The patient was assessed as skin type II. A dermoscopic close-up of a skin lesion. The chart notes a prior melanoma but no first-degree relative with melanoma.
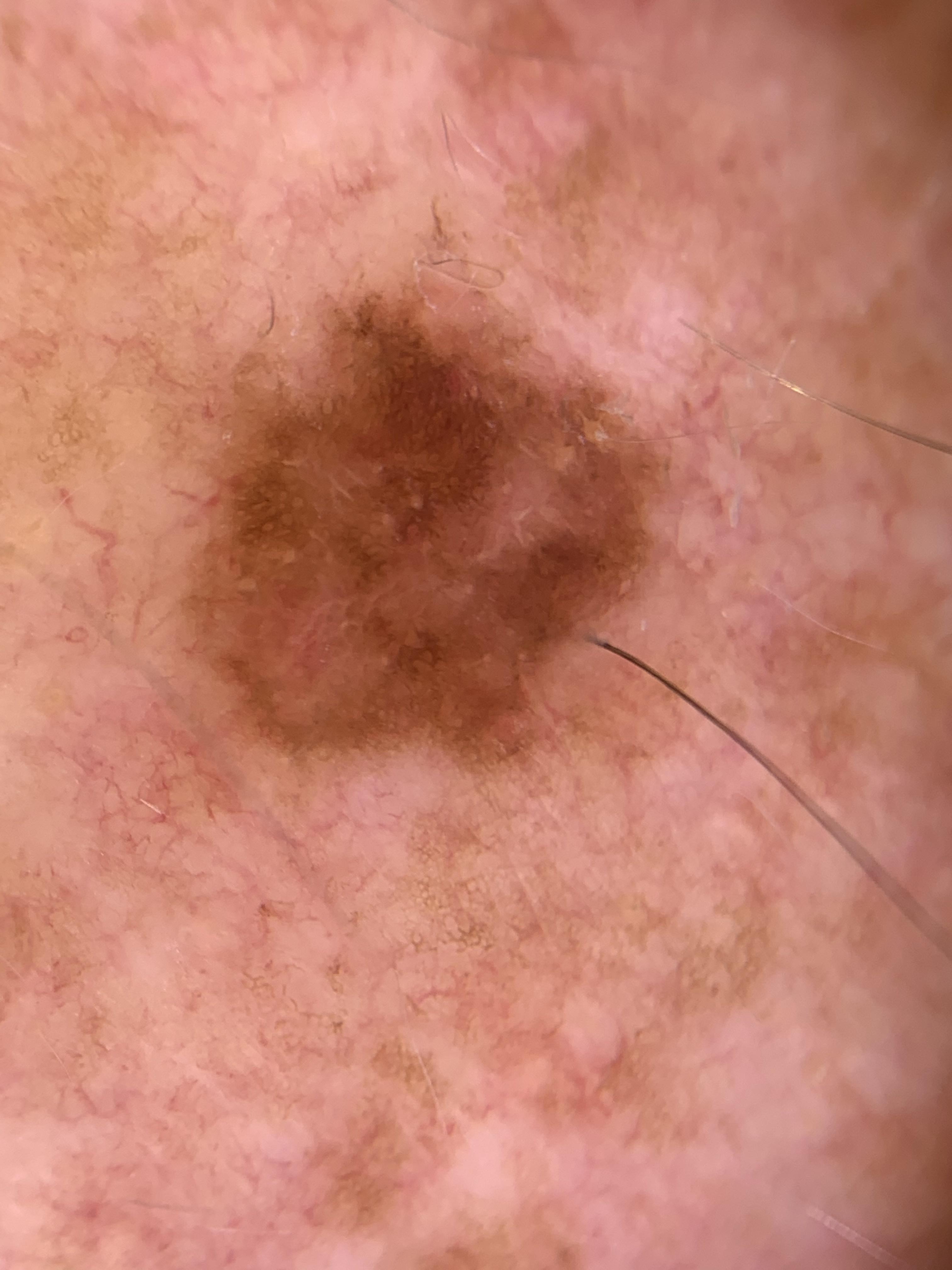{
  "lesion_location": {
    "region": "the trunk",
    "detail": "the posterior trunk"
  },
  "diagnosis": {
    "name": "Nevus",
    "malignancy": "benign",
    "confirmation": "histopathology",
    "lineage": "melanocytic"
  }
}